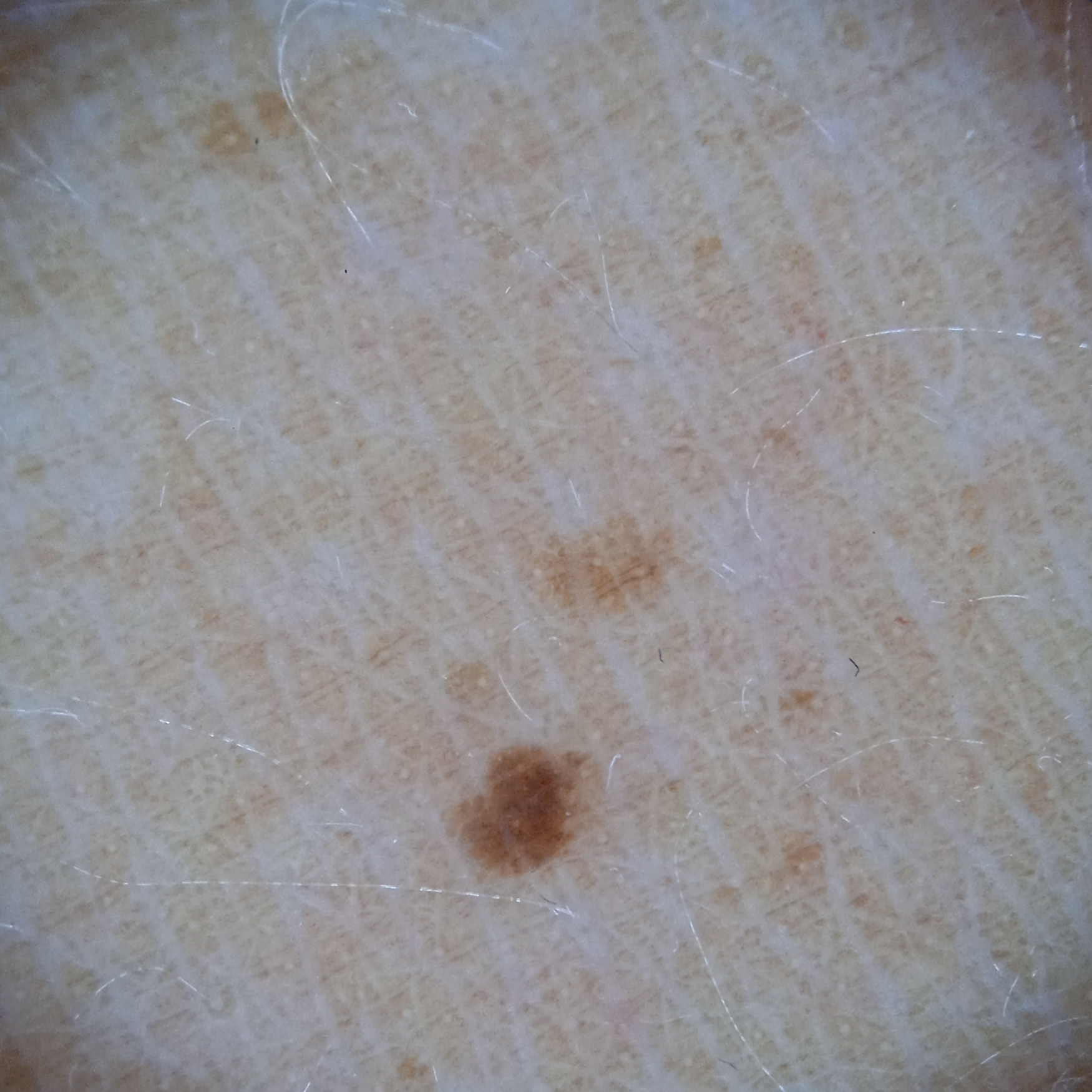Dermatologist review favored a melanocytic nevus.